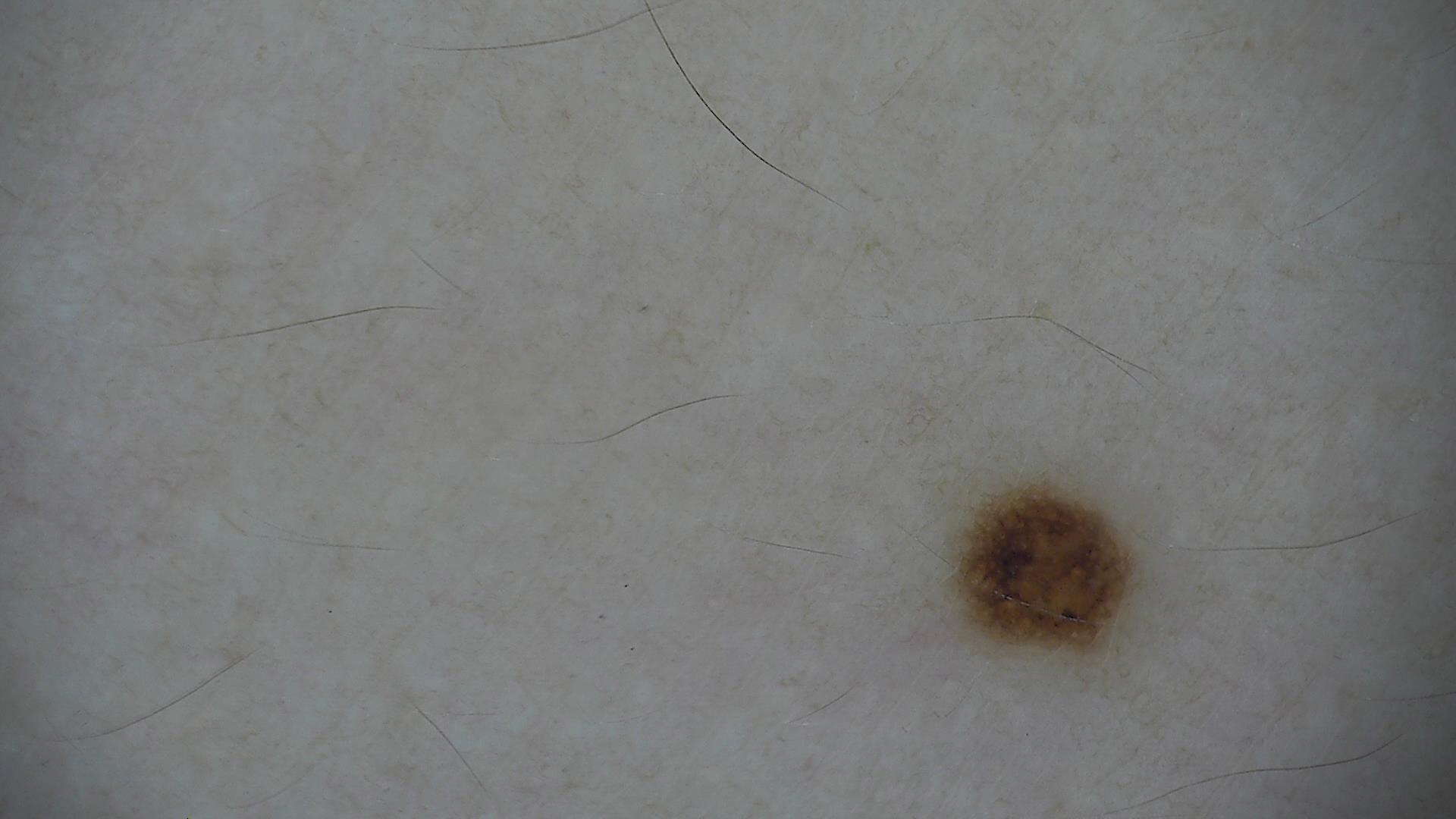<dermoscopy>
<image>dermatoscopy</image>
<diagnosis>
<name>dysplastic junctional nevus</name>
<code>jd</code>
<malignancy>benign</malignancy>
<super_class>melanocytic</super_class>
<confirmation>expert consensus</confirmation>
</diagnosis>
</dermoscopy>